An image taken at a distance: 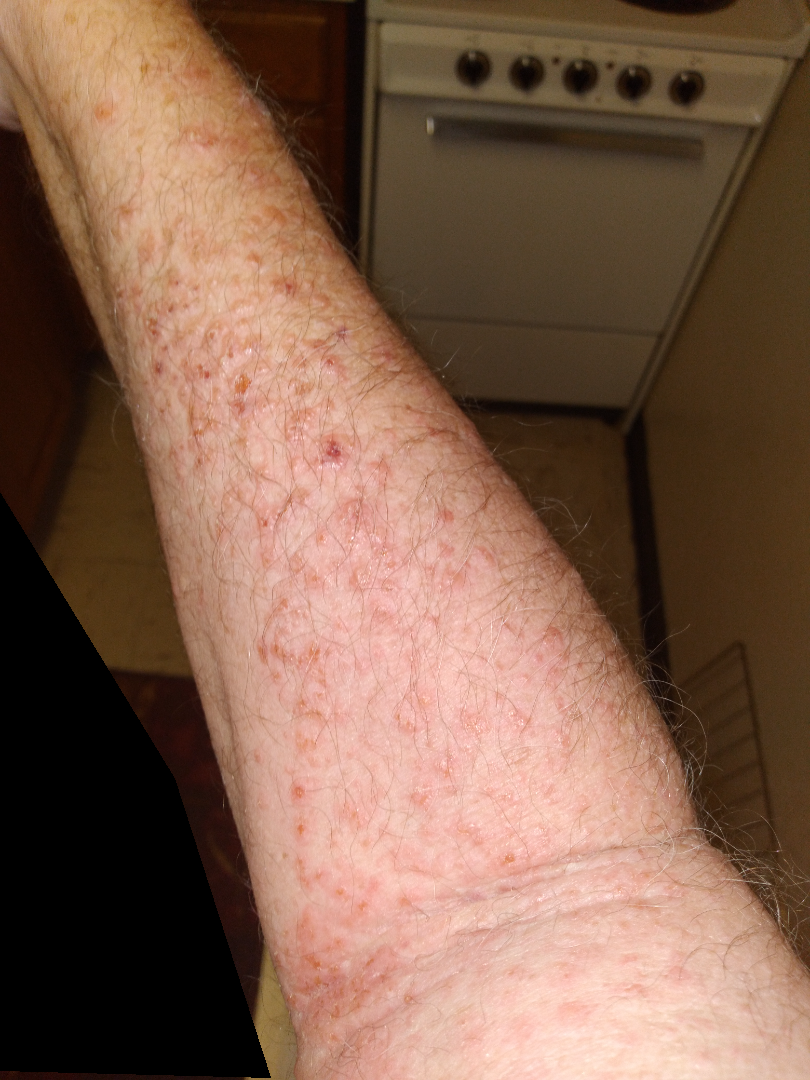| field | value |
|---|---|
| skin tone | Fitzpatrick II; non-clinician graders estimated 3 on the Monk skin tone scale |
| lesion texture | fluid-filled and raised or bumpy |
| dermatologist impression | Tinea (considered); Eczema (considered); Allergic Contact Dermatitis (considered) |